A dermoscopy image of a single skin lesion: 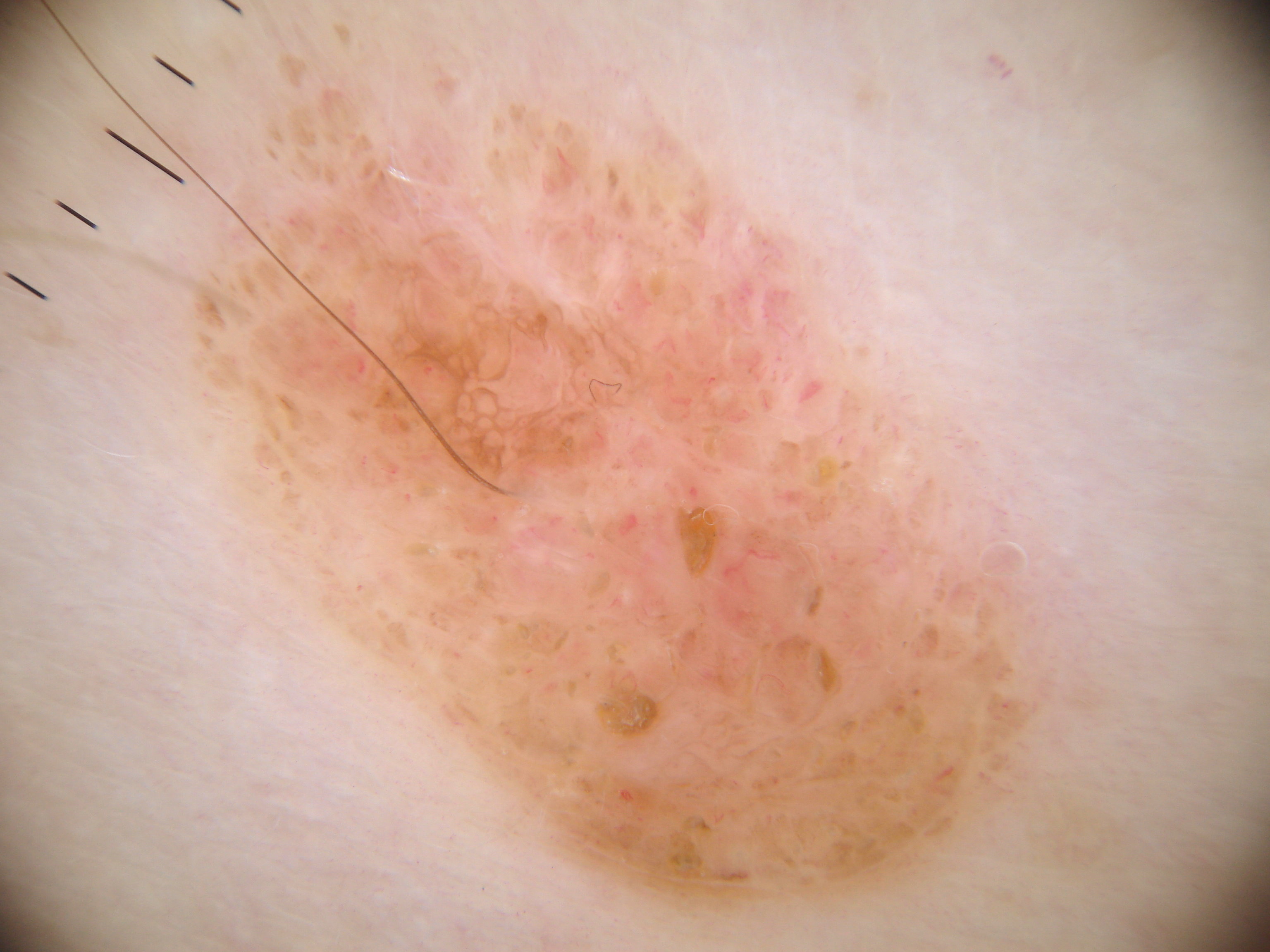| field | value |
|---|---|
| lesion location | 188/20/1067/908 |
| dermoscopic findings | globules and pigment network |
| assessment | a melanocytic nevus |